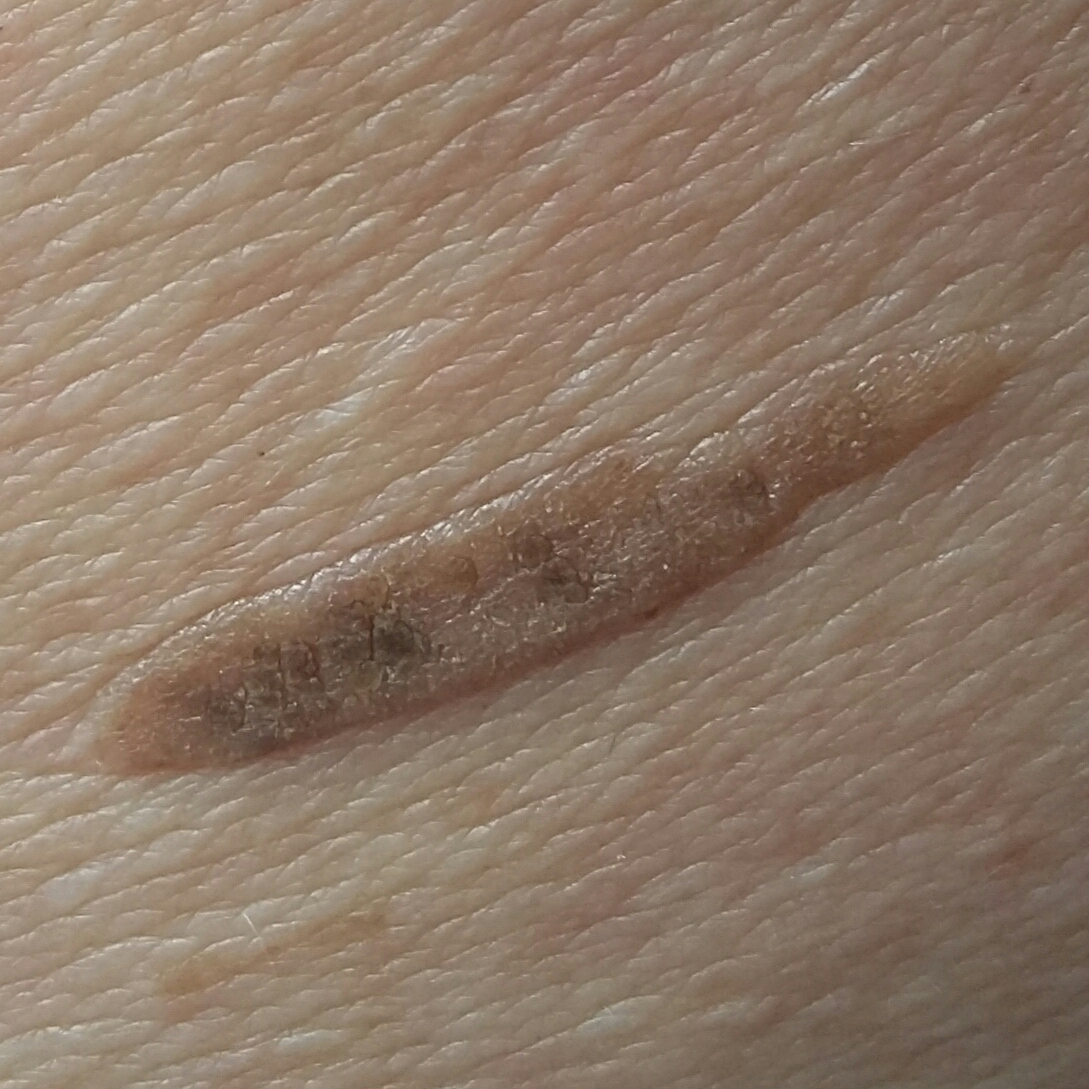Conclusion:
The consensus clinical diagnosis was a seborrheic keratosis.